The photograph was taken at a distance. The lesion involves the arm. The condition has been present for less than one week. The contributor is female. The patient notes itching. The patient notes the lesion is raised or bumpy. Self-categorized by the patient as a rash.
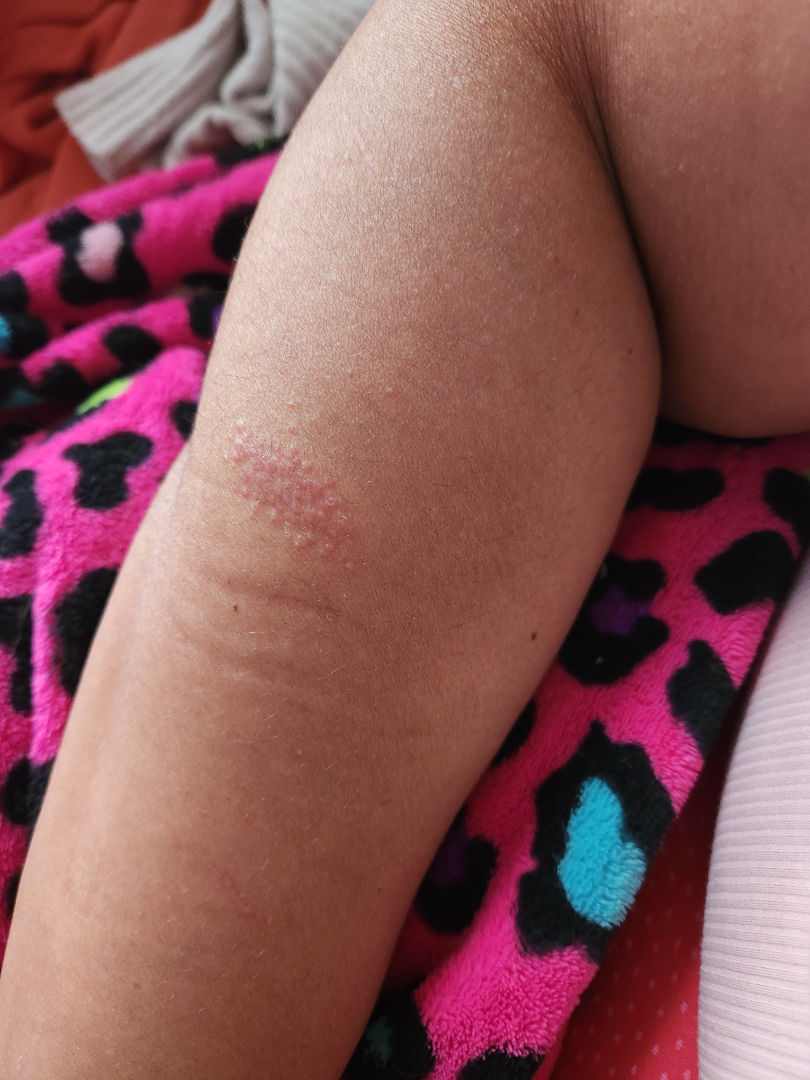Findings: On photographic review, most likely Eczema; also raised was Contact dermatitis; an alternative is Psoriasis.